A male patient age 72; a dermoscopic image of a skin lesion; the patient says their skin reddens with sun exposure; few moles overall by the patient's own estimate; imaged for a research study, with no referral diagnosis recorded; by self-report, a personal history of cancer and no immunosuppression: 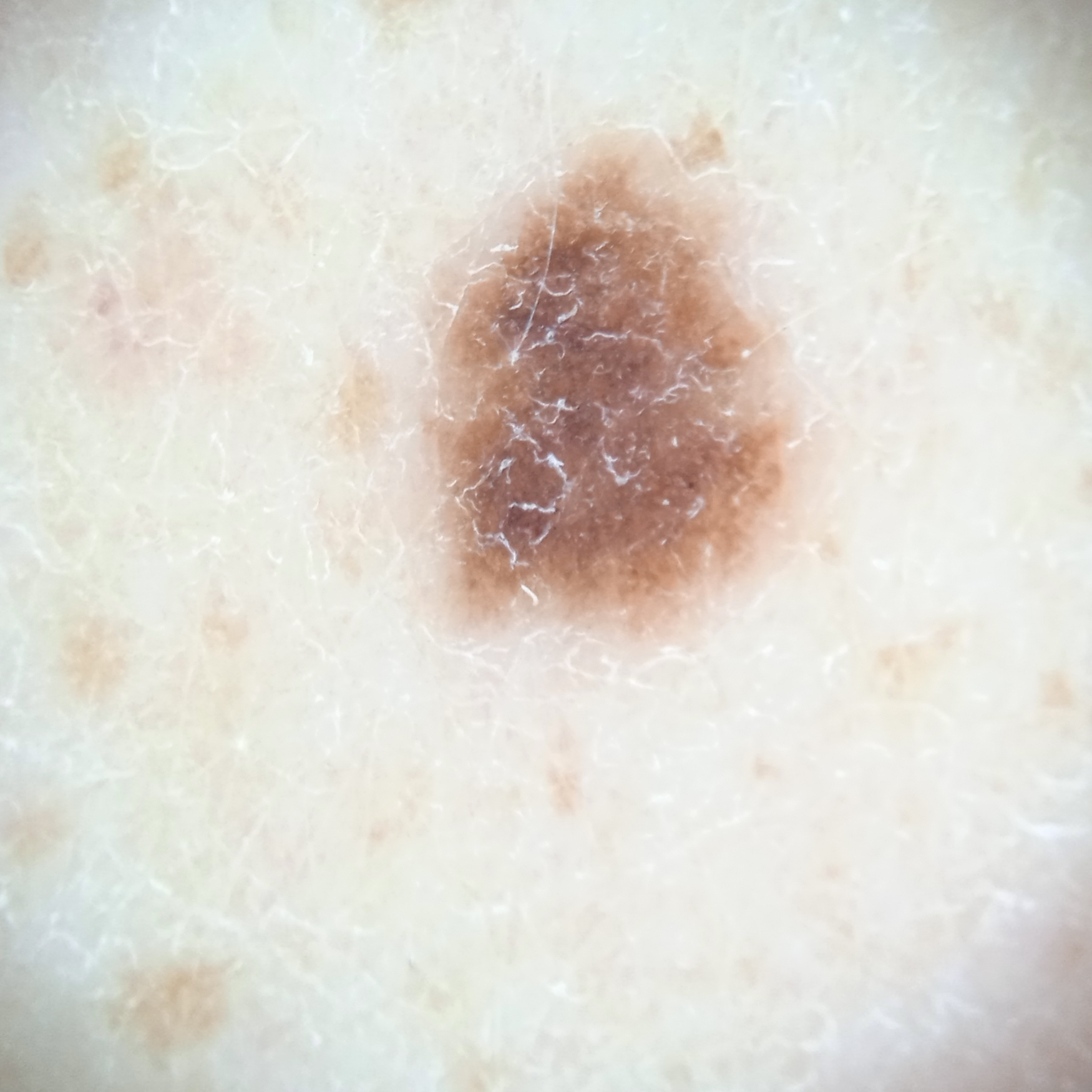- body site · the back
- diameter · 5.6 mm
- diagnosis · melanocytic nevus (dermatologist consensus)